A dermatoscopic image of a skin lesion.
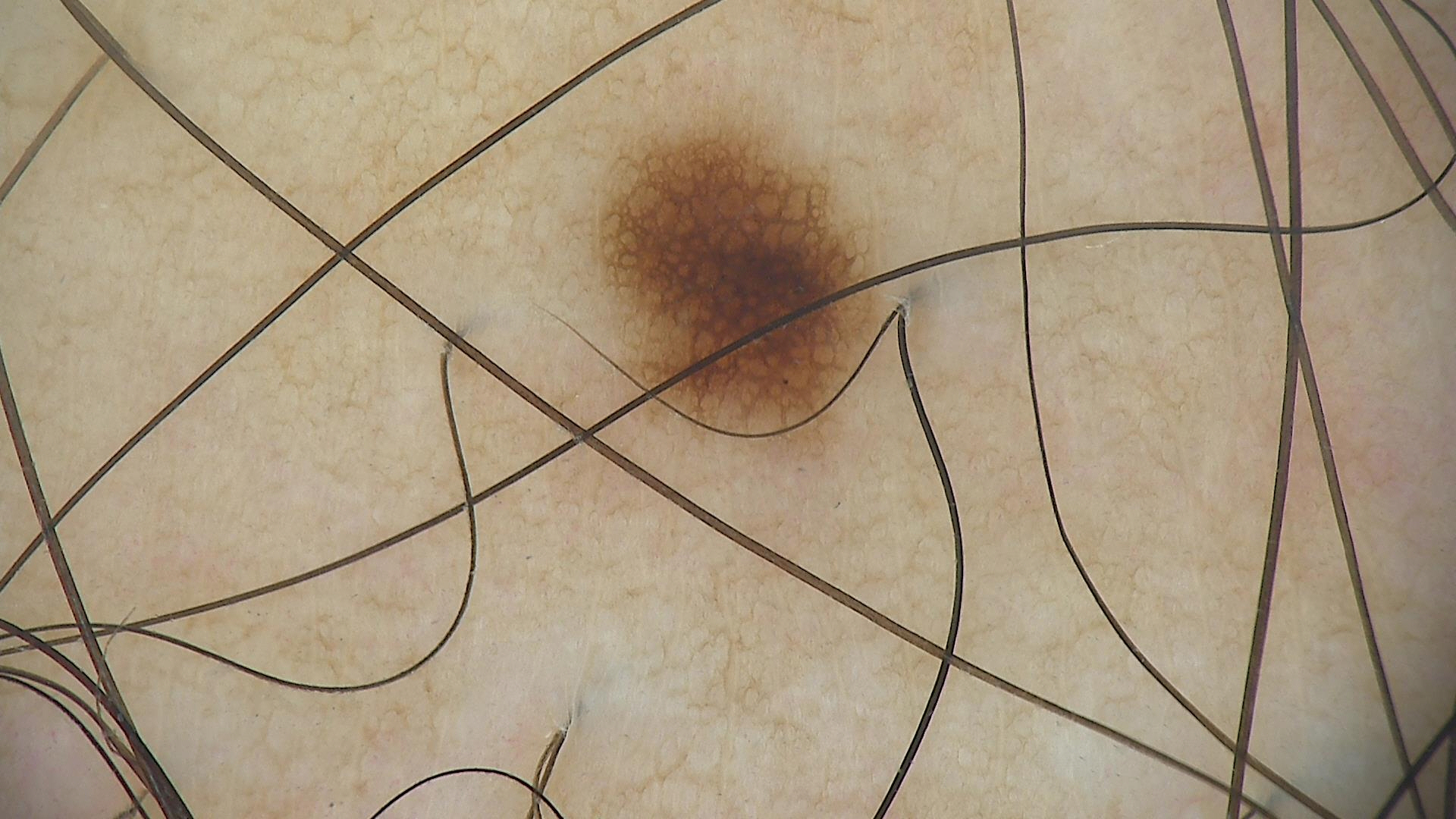Case:
* assessment: dysplastic junctional nevus (expert consensus)